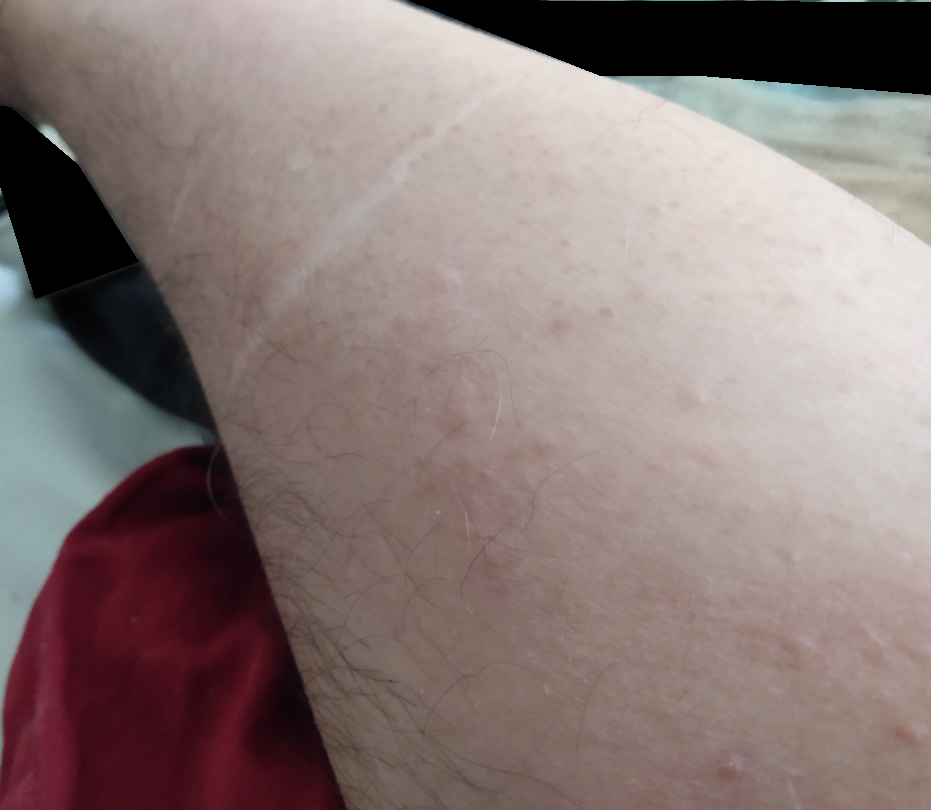Impression: The reviewer was unable to grade this case for skin condition. History: Texture is reported as raised or bumpy. This image was taken at a distance. Male contributor, age 40–49. Located on the arm. Self-categorized by the patient as a rash. The contributor reports burning and itching.